The lesion involves the back of the hand, leg and arm; a close-up photograph; the contributor is a male aged 40–49: 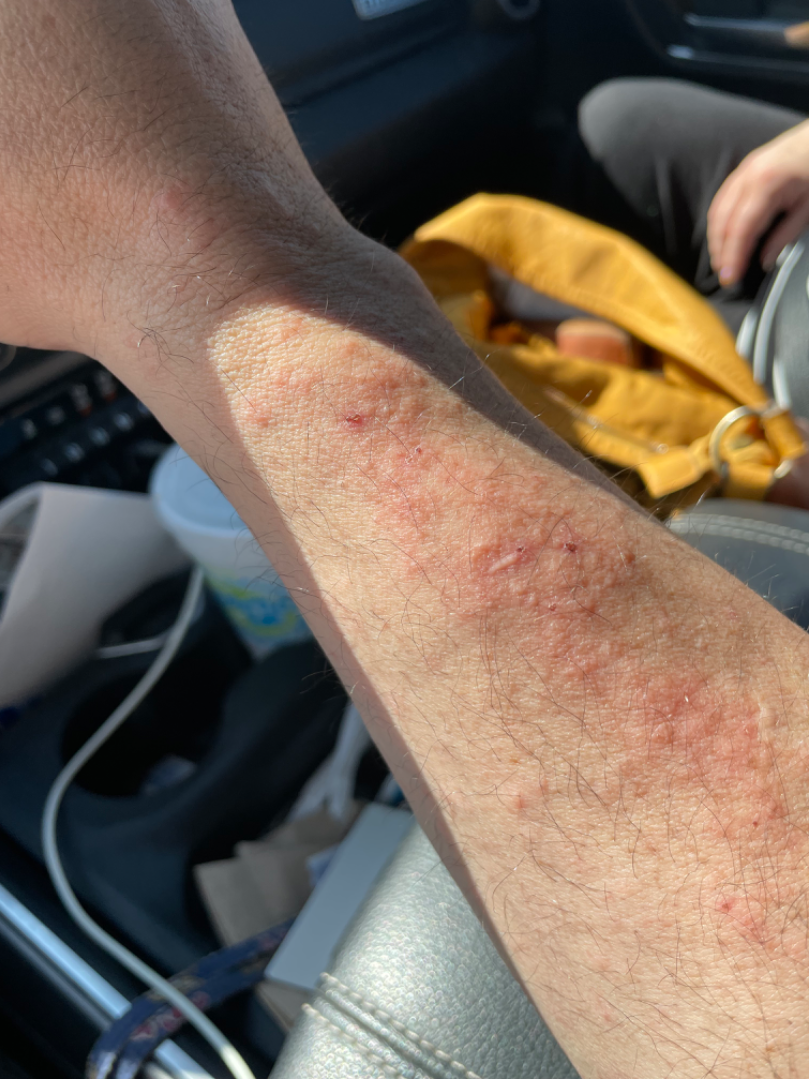Findings:
On teledermatology review: favoring Eczema.